A clinical photograph showing a skin lesion; a moderate number of moles by the patient's own estimate; the patient says their skin reddens painfully with sun exposure; a female patient 81 years of age; collected as part of a research study, without a referral diagnosis.
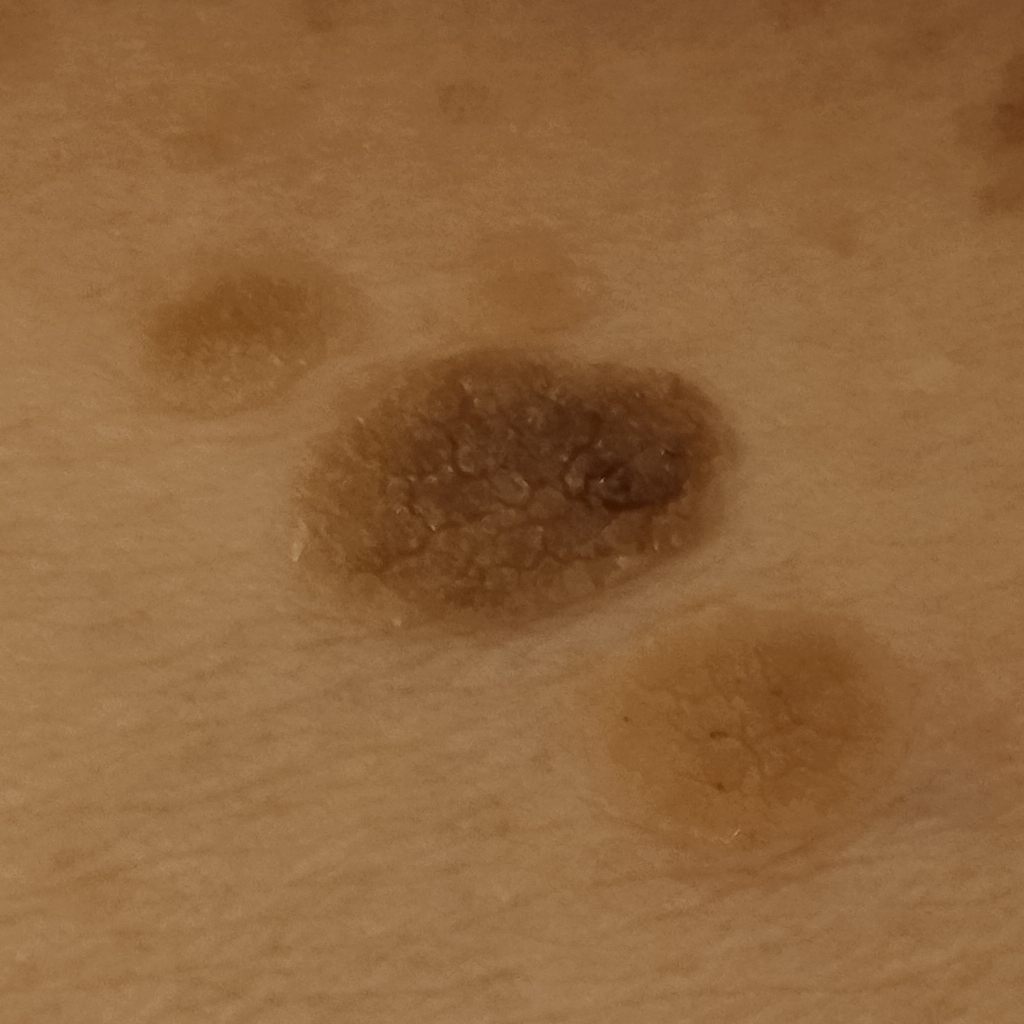Clinical context: The lesion measures approximately 12.2 mm. Conclusion: The consensus diagnosis for this lesion was a seborrheic keratosis.